A dermoscopic photograph of a skin lesion:
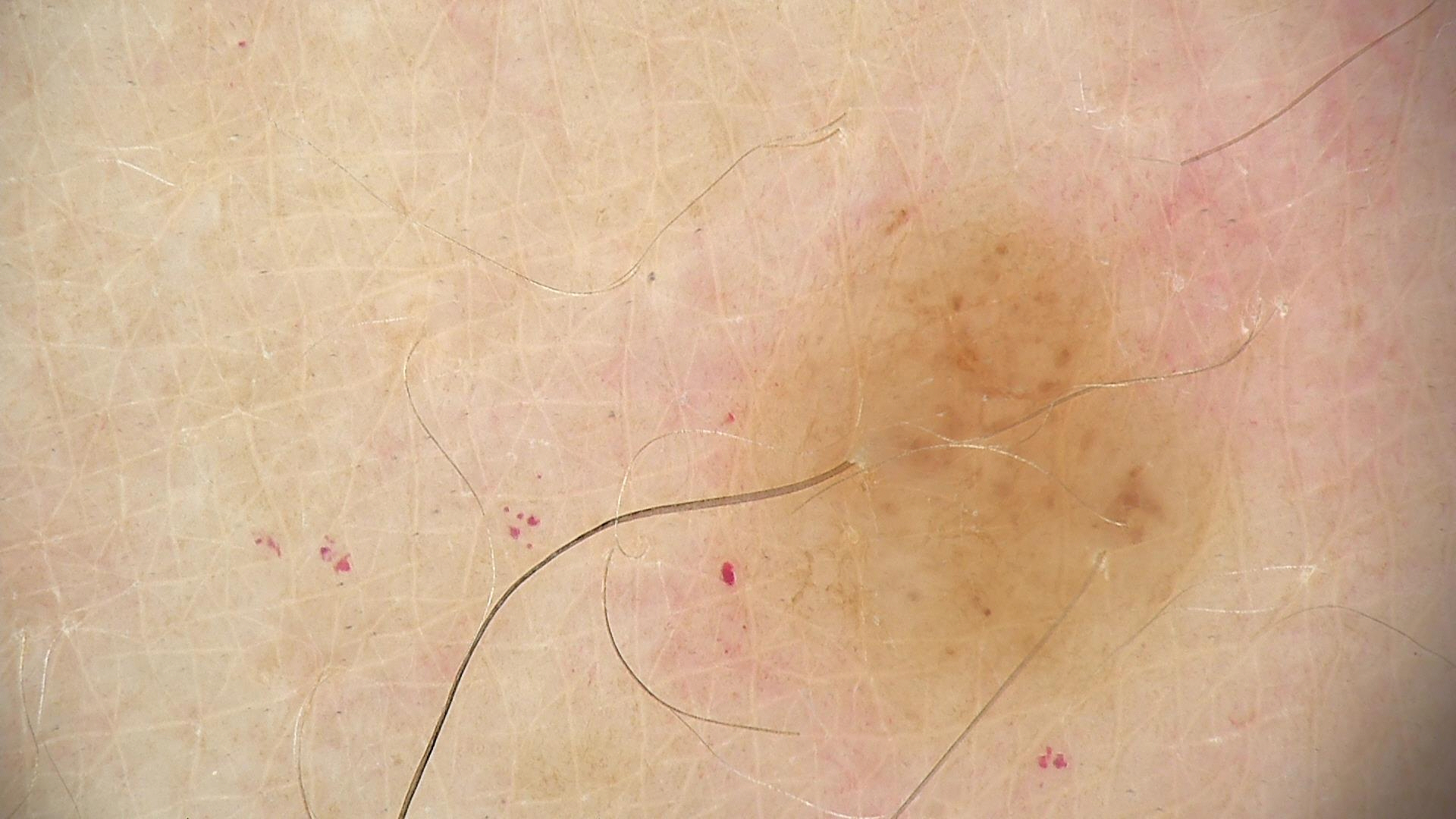Impression:
Consistent with a banal lesion — a dermal nevus.